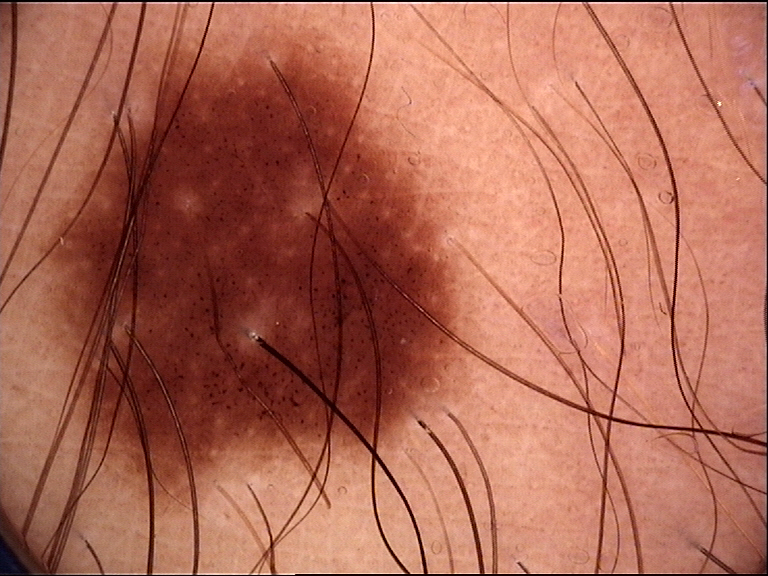Impression: Labeled as a benign lesion — a dysplastic junctional nevus.